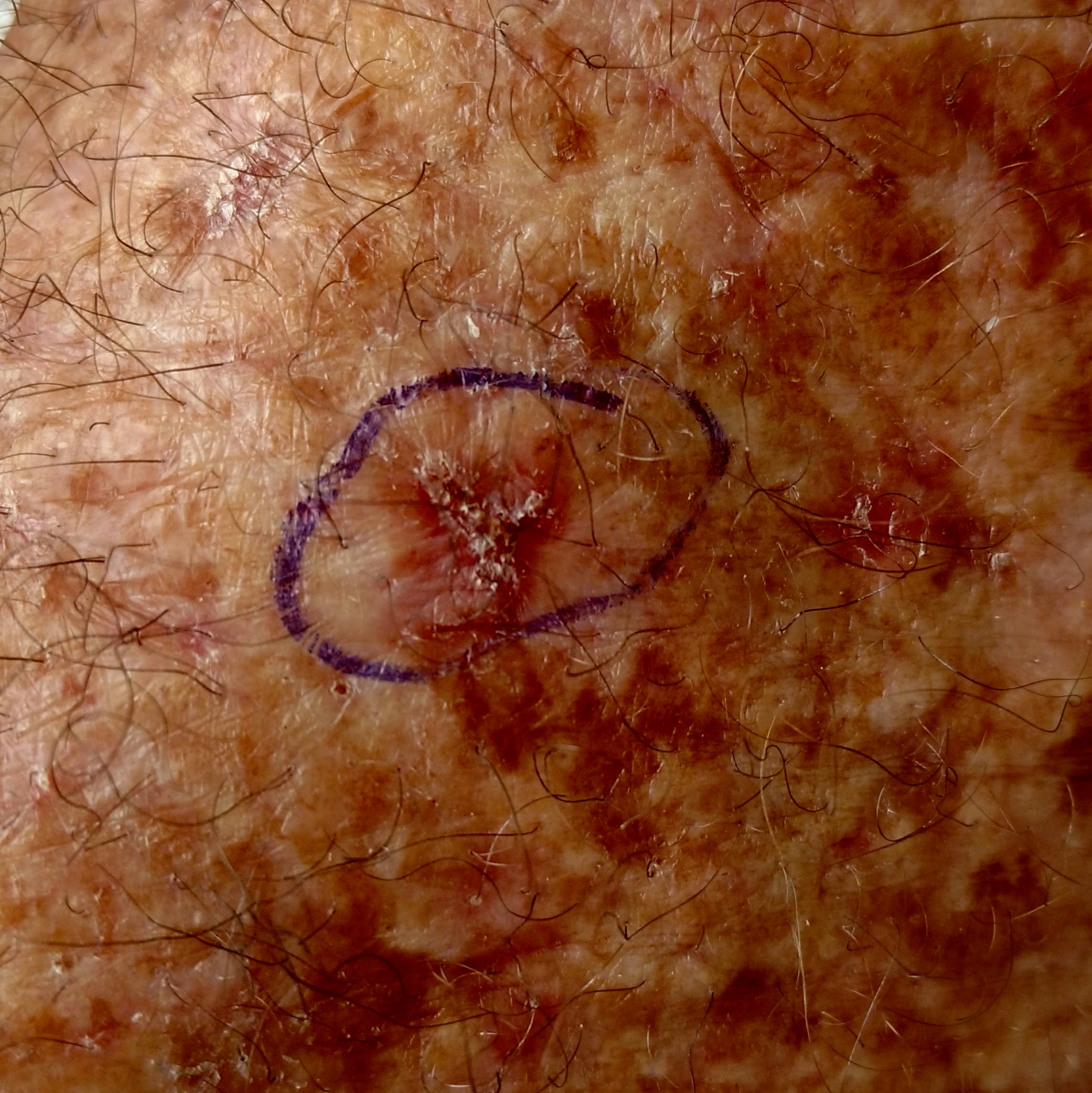A clinical close-up photograph of a skin lesion.
A patient in their 70s.
Located on a forearm.
The patient reports that the lesion has bled and itches.
Expert review favored an actinic keratosis.